Close-up view, the subject is a female aged 30–39, located on the back of the hand — 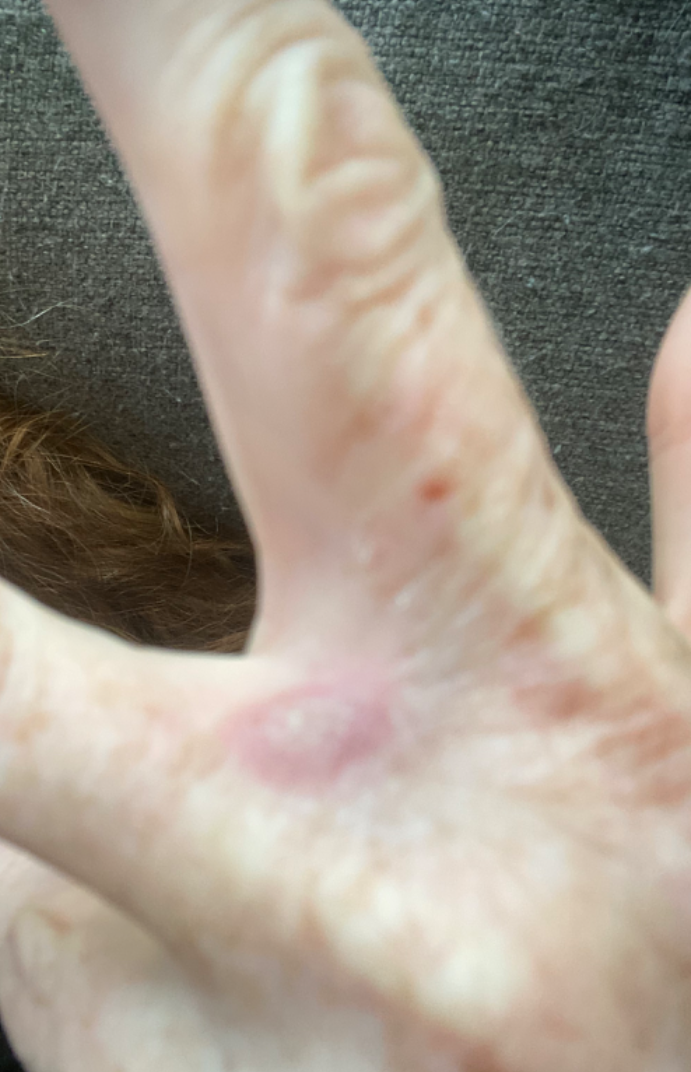assessment: indeterminate from the photograph